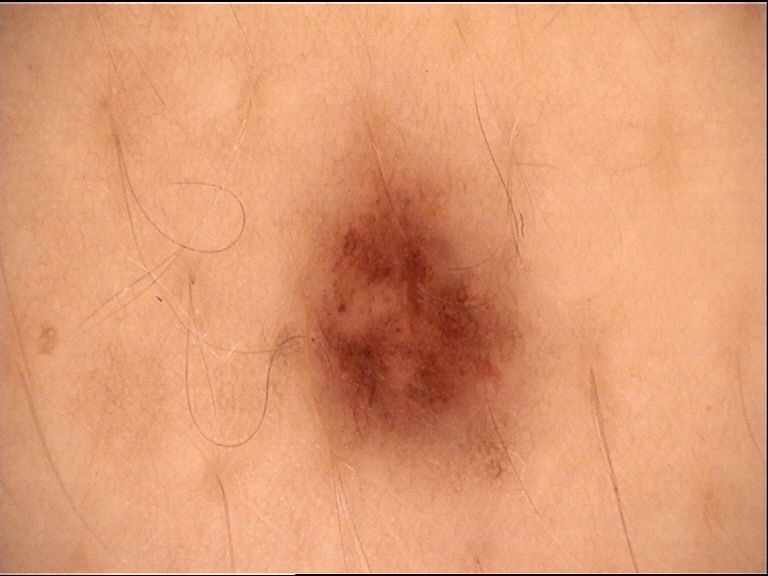diagnostic label=dysplastic junctional nevus (expert consensus)